The lesion involves the front of the torso; the condition has been present for one to three months; a close-up photograph: 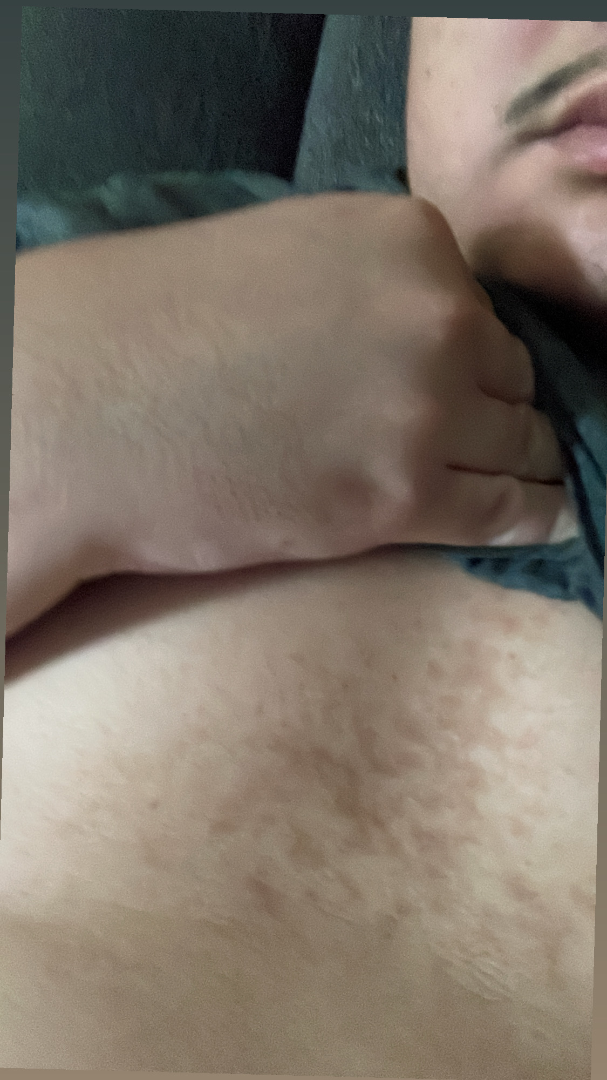On teledermatology review: in keeping with Confluent and reticulate papillomatosis.